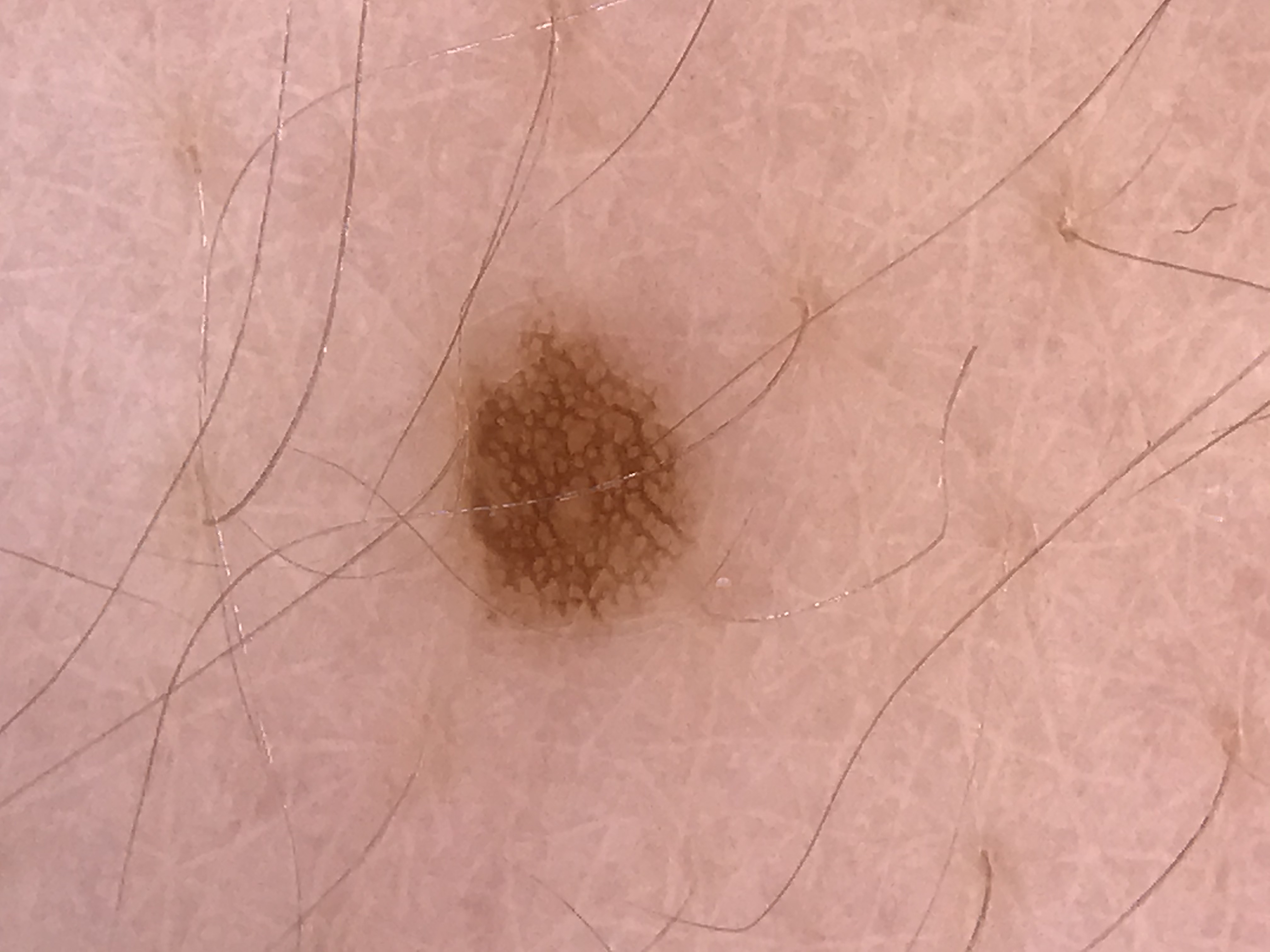image type: dermoscopy | subtype: banal | label: junctional nevus (expert consensus).